A dermoscopic image of a skin lesion:
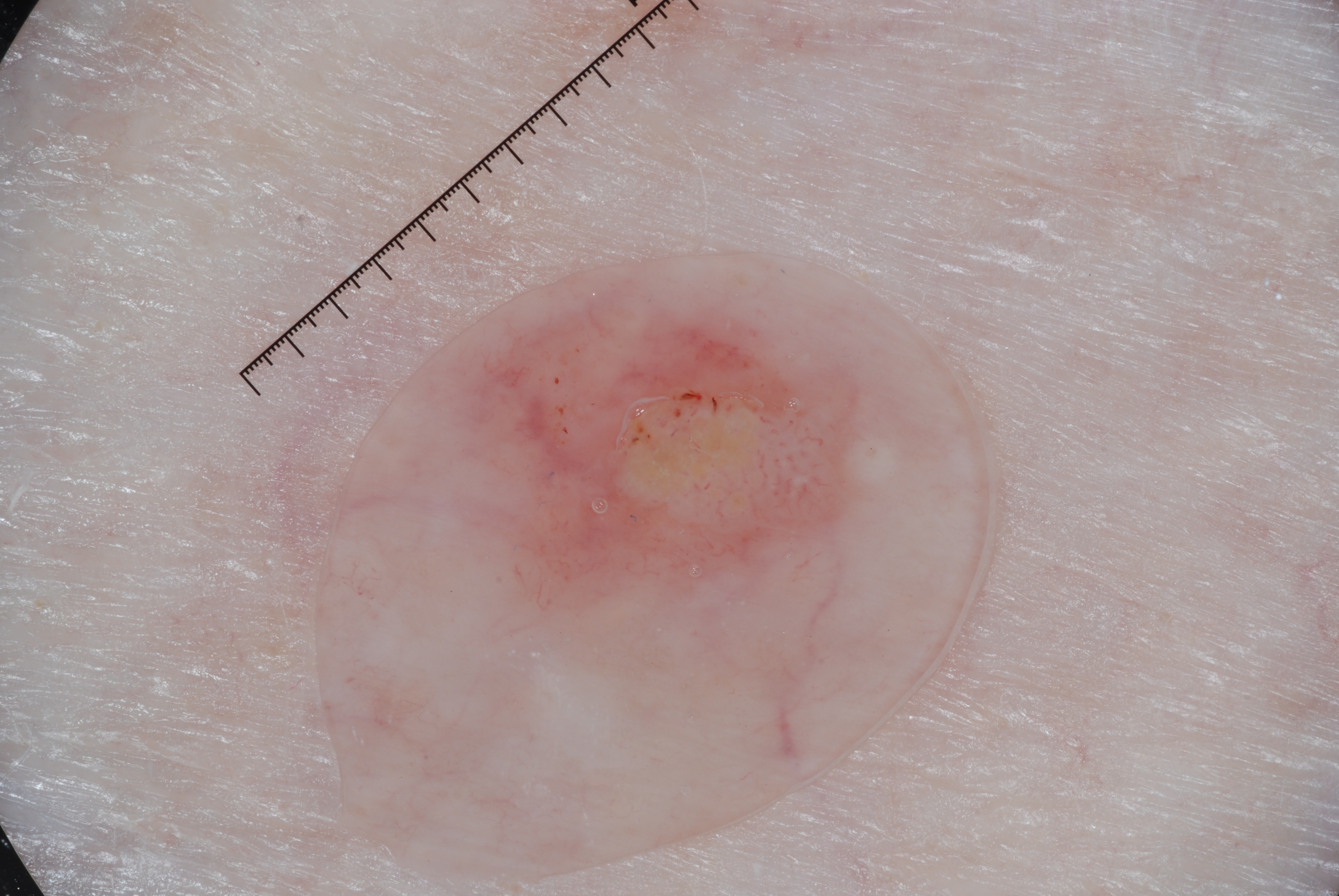With coordinates (x1, y1, x2, y2), the lesion's extent is bbox=[436, 289, 926, 641]. The clinical diagnosis was a seborrheic keratosis, a benign lesion.